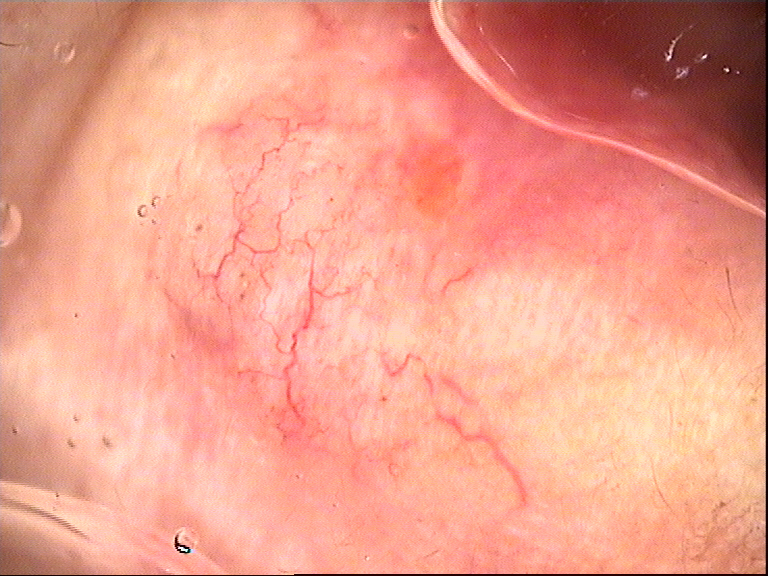image type = dermoscopy | diagnostic label = basal cell carcinoma (biopsy-proven).